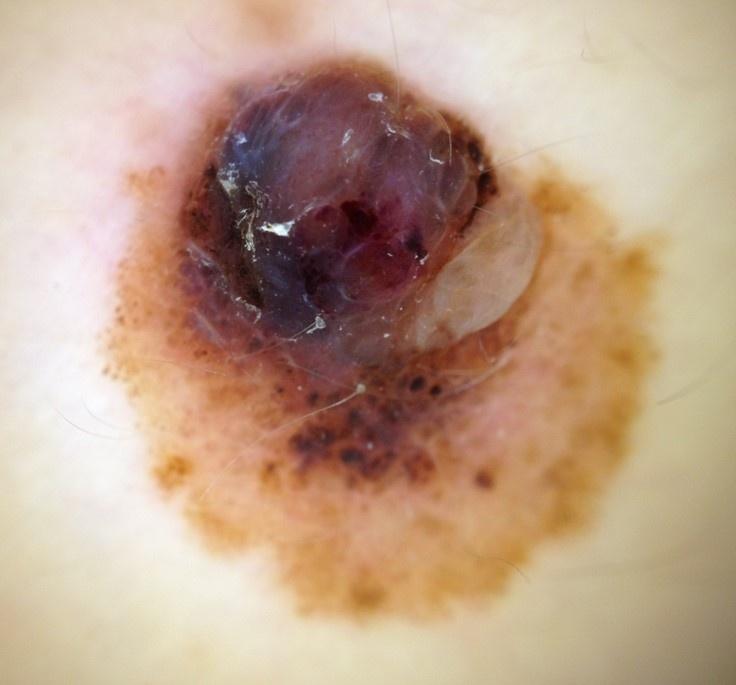Contact-polarized dermoscopy of a skin lesion.
A female subject roughly 40 years of age.
The lesion is located on an upper extremity.
Biopsy-confirmed as a melanoma.